Dermoscopy of a skin lesion: 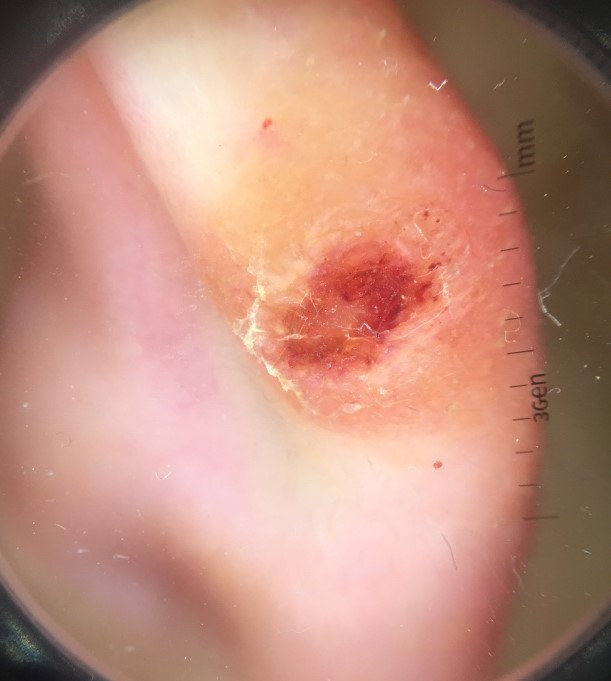lesion type: keratinocytic; class: squamous cell carcinoma (biopsy-proven).